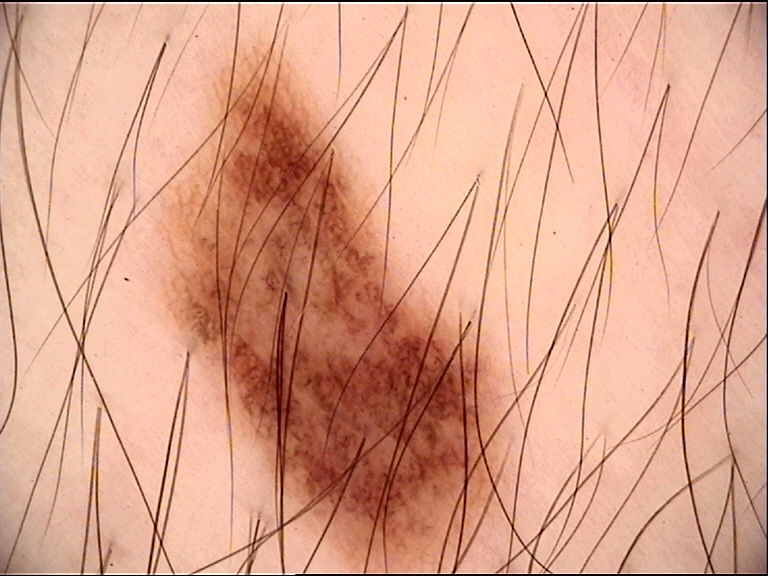Classified as a benign lesion — a dysplastic junctional nevus.